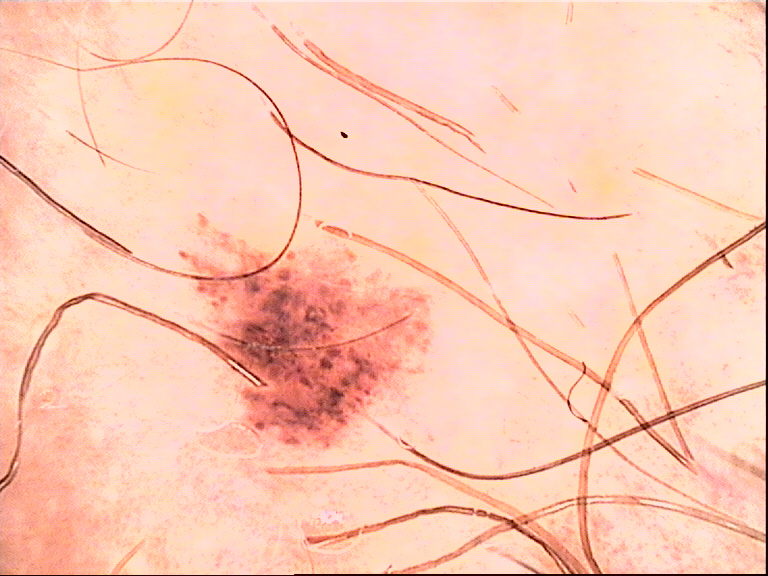Diagnosed as a dysplastic junctional nevus.